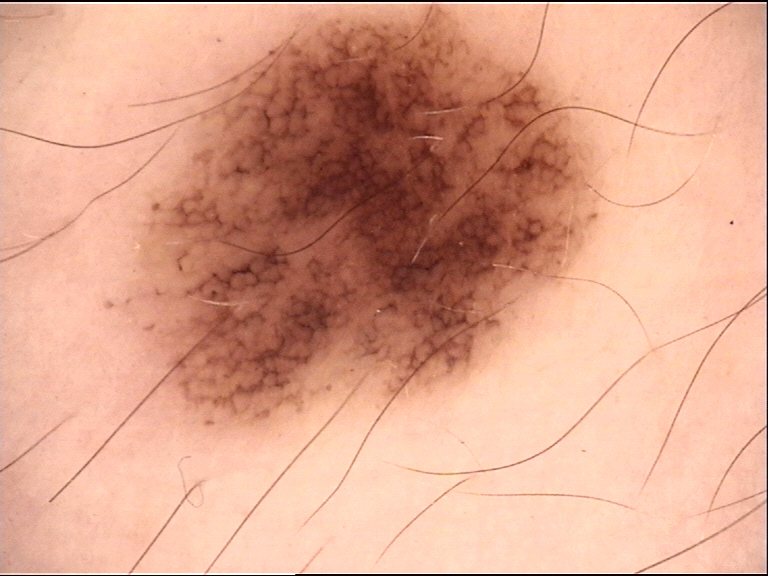A dermoscopic photograph of a skin lesion.
Diagnosed as a benign lesion — a dysplastic junctional nevus.